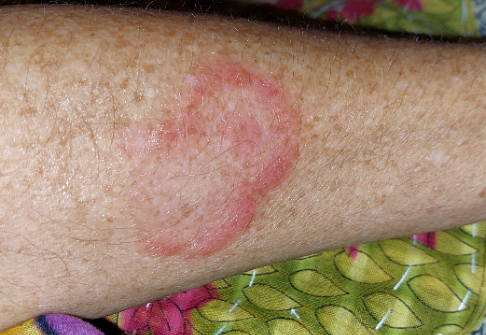assessment: not assessable.